A dermoscopy image of a single skin lesion: 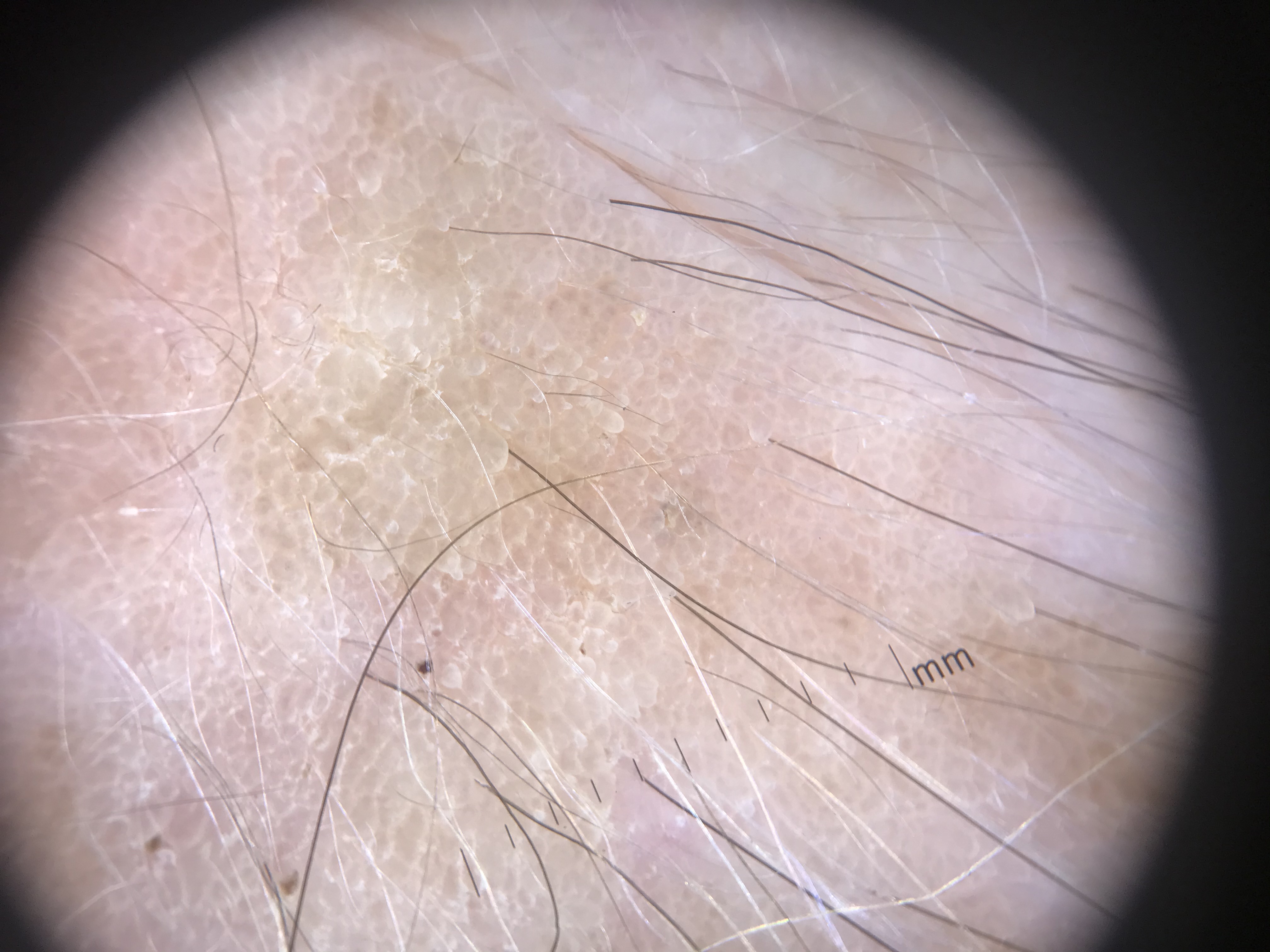The diagnostic label was a keratinocytic, benign lesion — a seborrheic keratosis.